The photo was captured at an angle. The arm is involved:
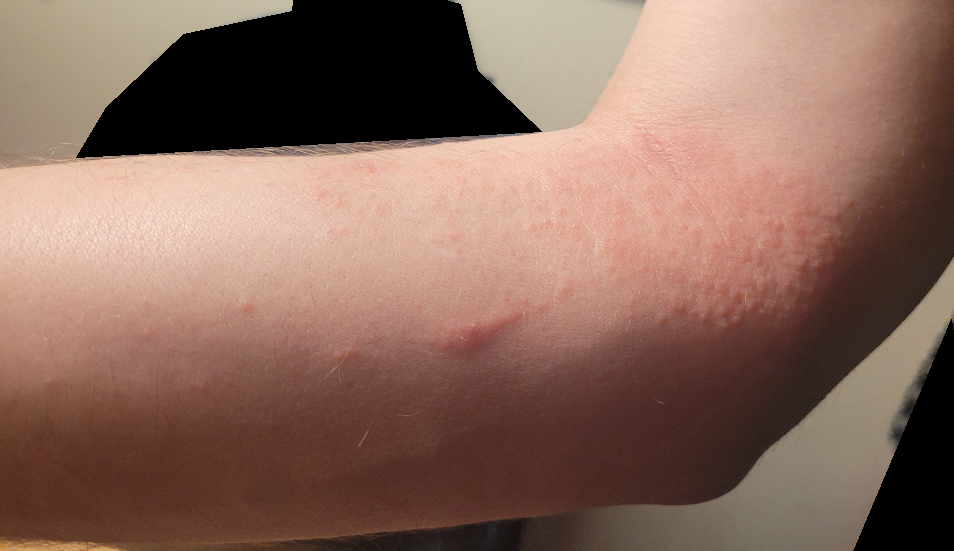{
  "patient_category": "a rash",
  "systemic_symptoms": "none reported",
  "texture": "raised or bumpy",
  "duration": "less than one week",
  "skin_tone": {
    "fitzpatrick": "III"
  },
  "differential": {
    "Acute and chronic dermatitis": 0.5,
    "Allergic Contact Dermatitis": 0.5
  }
}